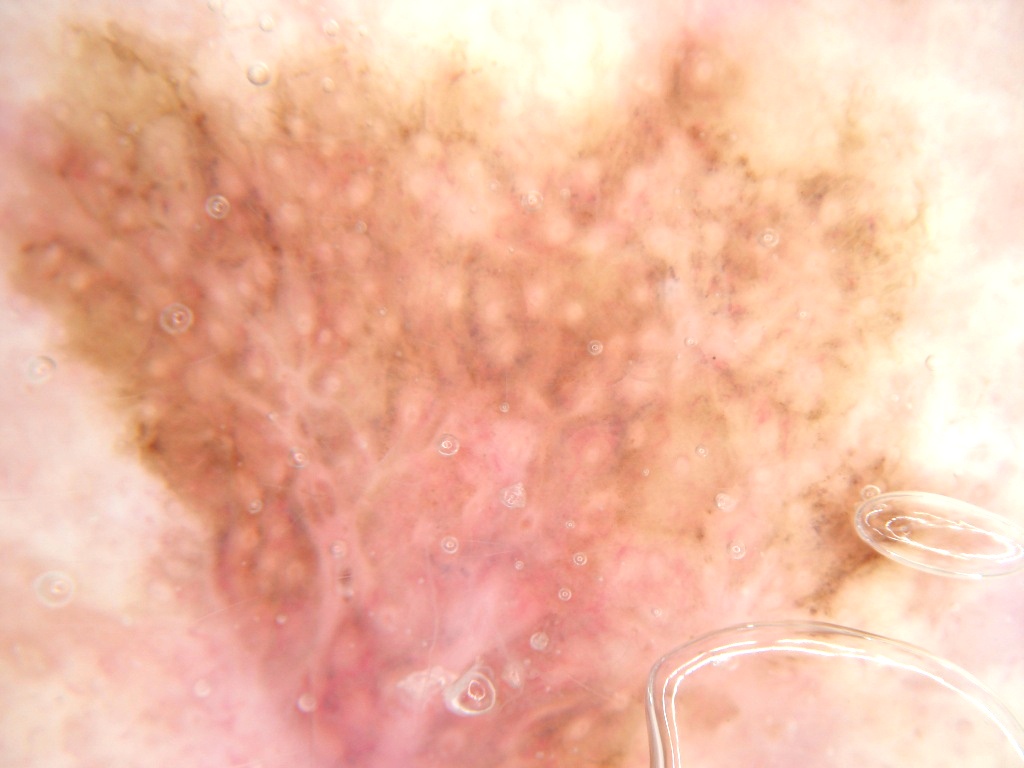A dermatoscopic image of a skin lesion.
The lesion spans essentially the entire dermoscopic field.
Histopathology confirmed a malignant skin lesion.